A skin lesion imaged with a dermatoscope:
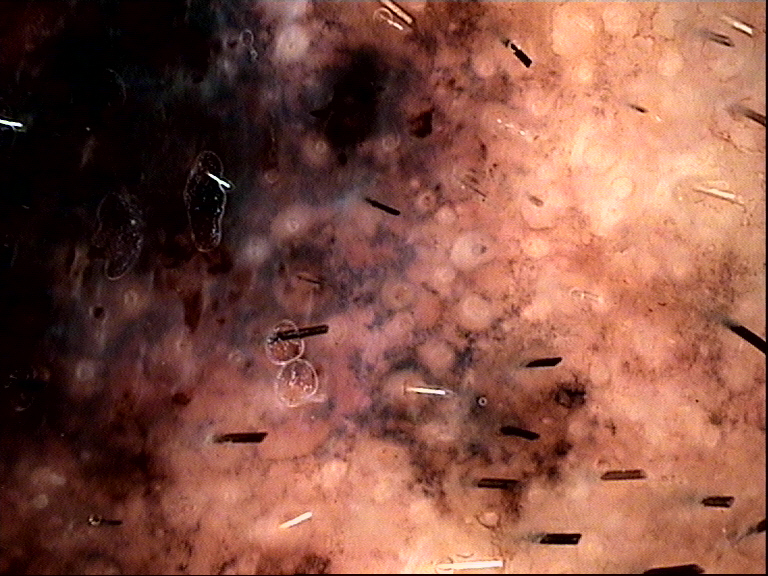Conclusion: The biopsy diagnosis was a malignant lesion — a lentigo maligna melanoma.